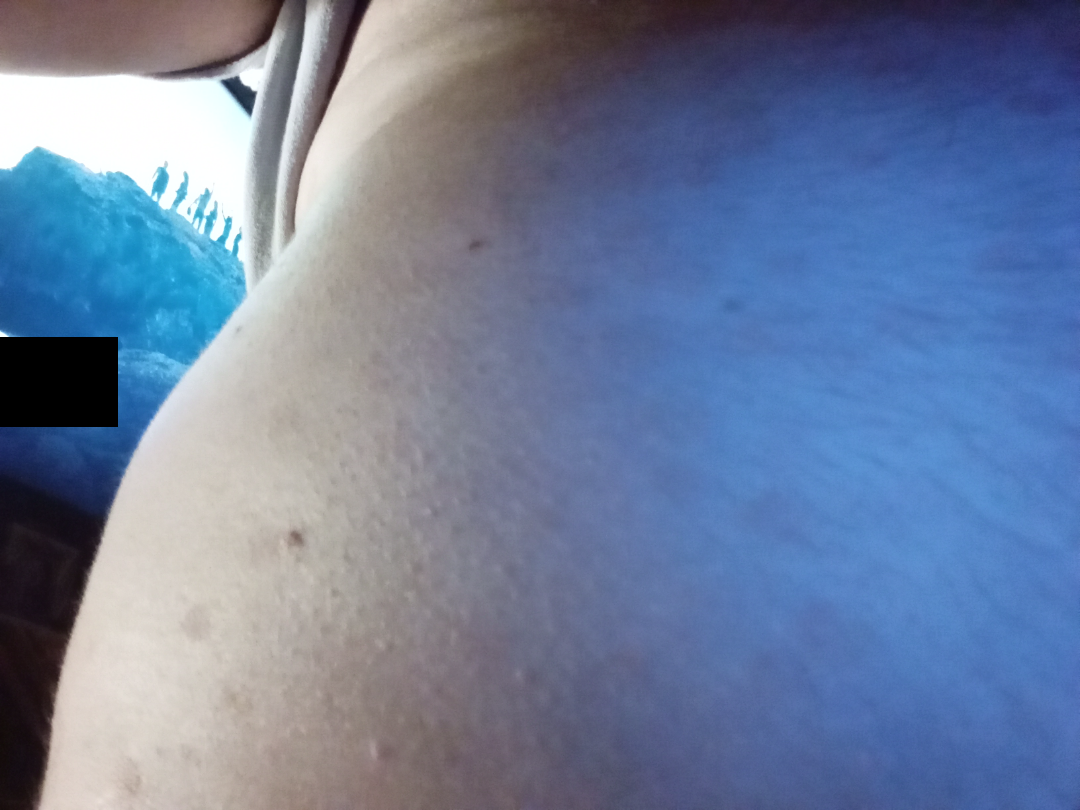{"shot_type": "at an angle", "differential": {"leading": ["Tinea Versicolor"], "considered": ["Tinea", "Eczema"]}}